The lesion is associated with itching, burning and bleeding · the photograph was taken at an angle · the affected area is the head or neck · the lesion is described as rough or flaky.
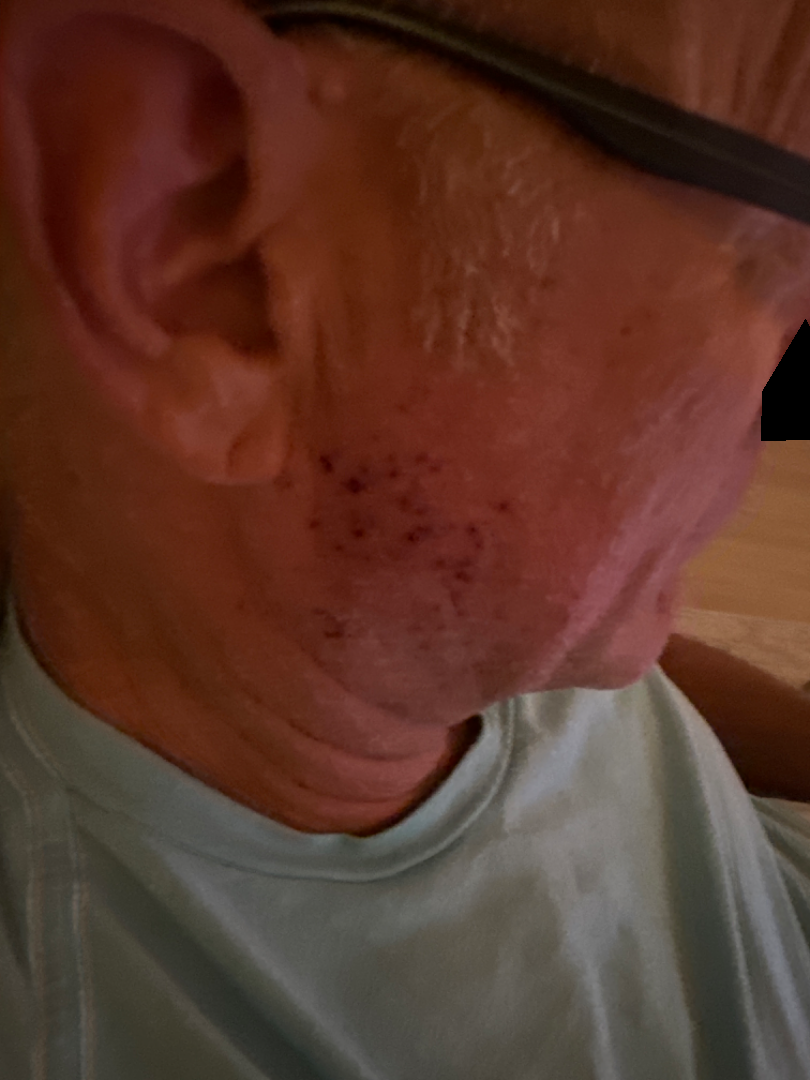The skin condition could not be confidently assessed from this image.